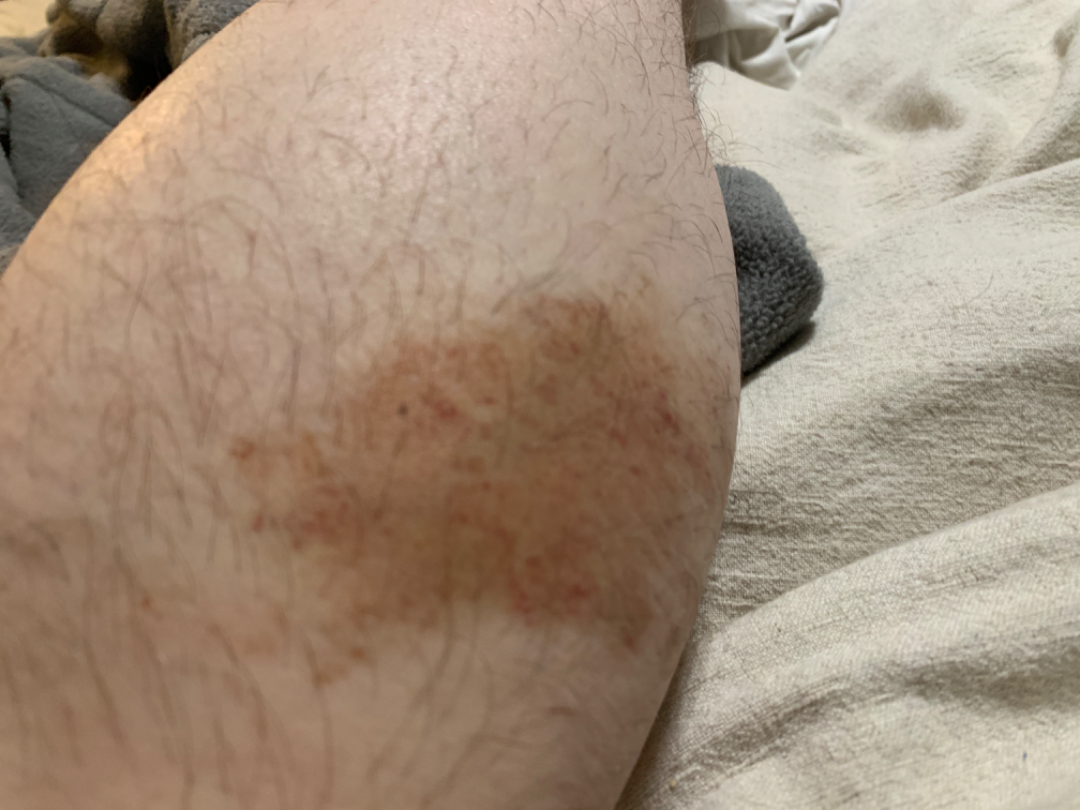differential:
  tied_lead:
    - Pigmented purpuric eruption
    - Irritant Contact Dermatitis